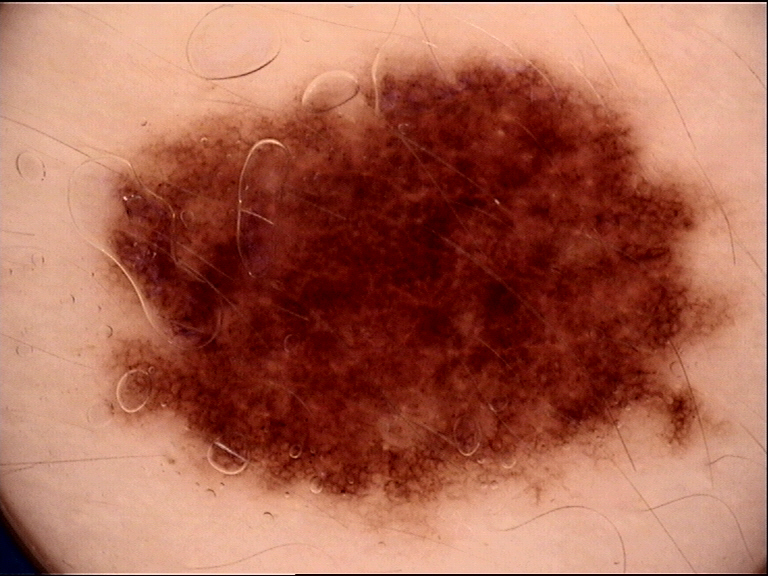Q: What kind of image is this?
A: dermatoscopy
Q: What is the diagnosis?
A: dysplastic junctional nevus (expert consensus)